A dermoscopy image of a single skin lesion — 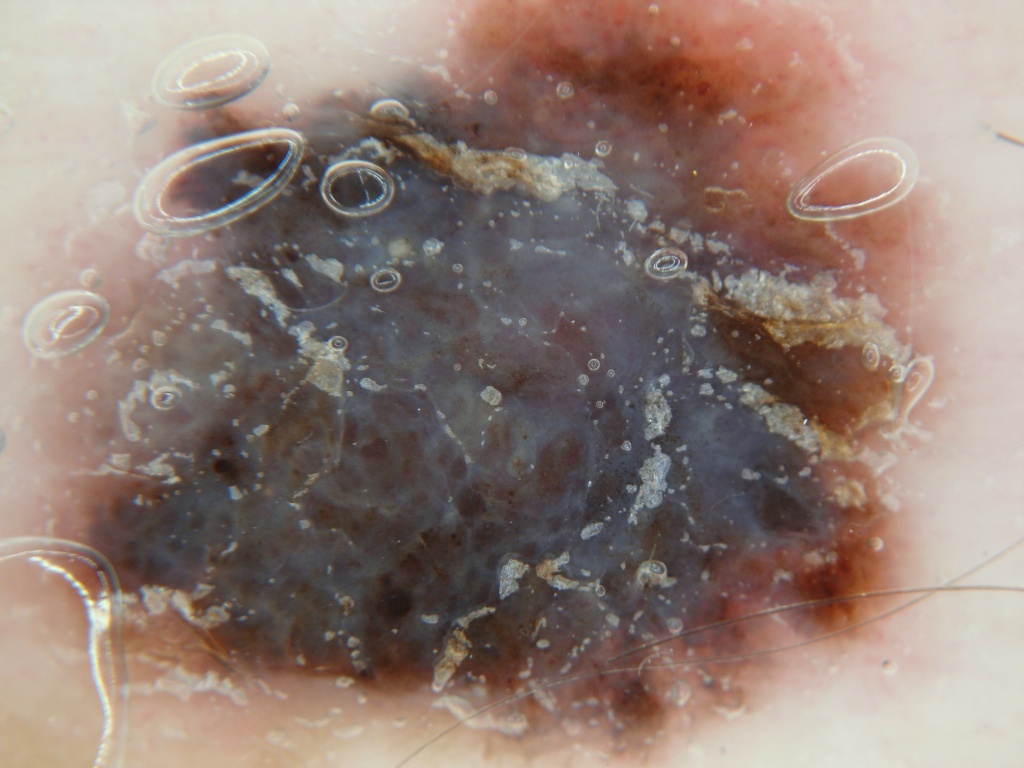Q: Which dermoscopic features are absent?
A: globules, milia-like cysts, negative network, streaks, and pigment network
Q: Where is the lesion located?
A: spans the dermoscopic field
Q: What is this lesion?
A: a melanoma, a malignant skin lesion